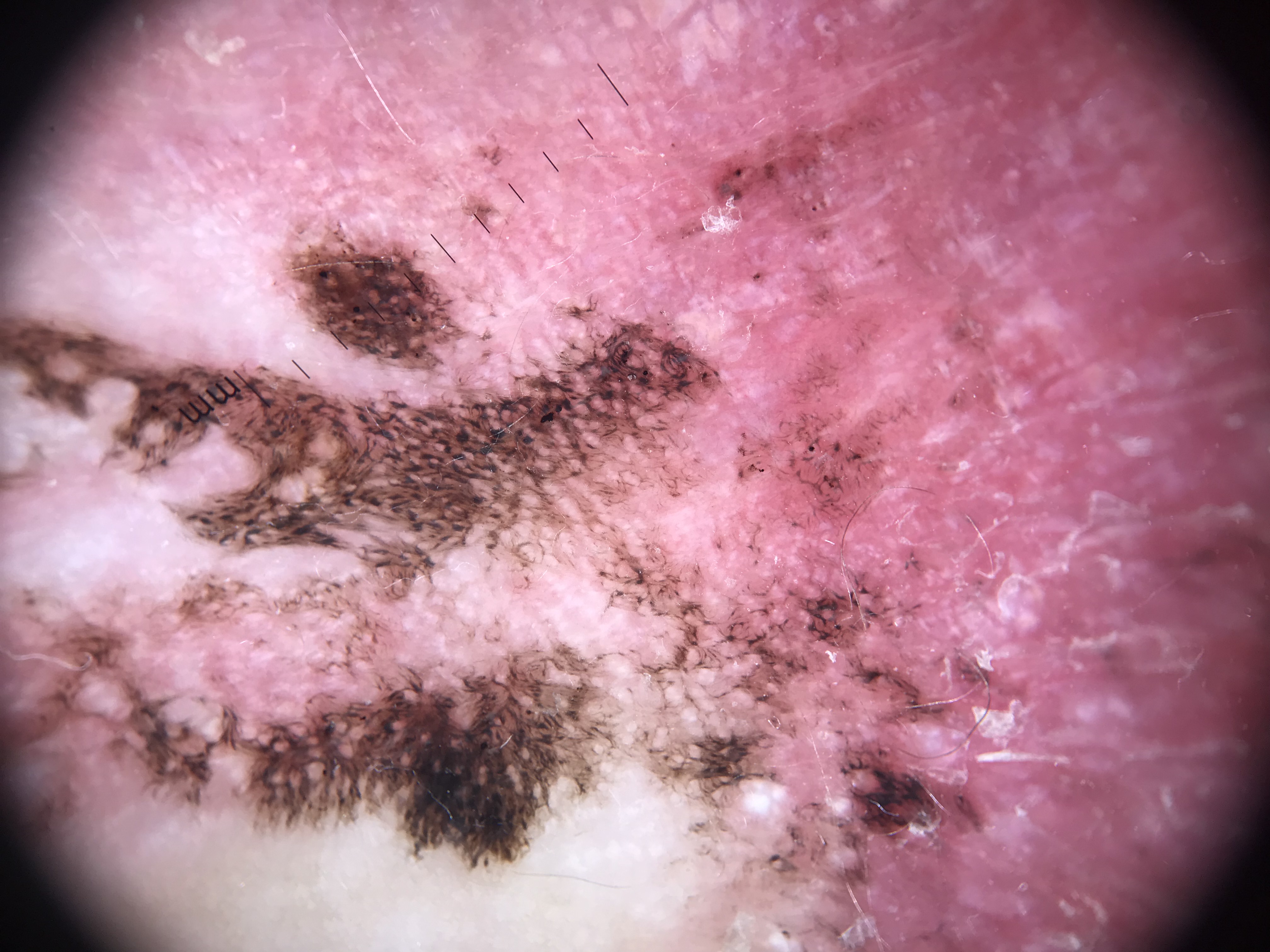image=dermatoscopy; class=melanoma (biopsy-proven).